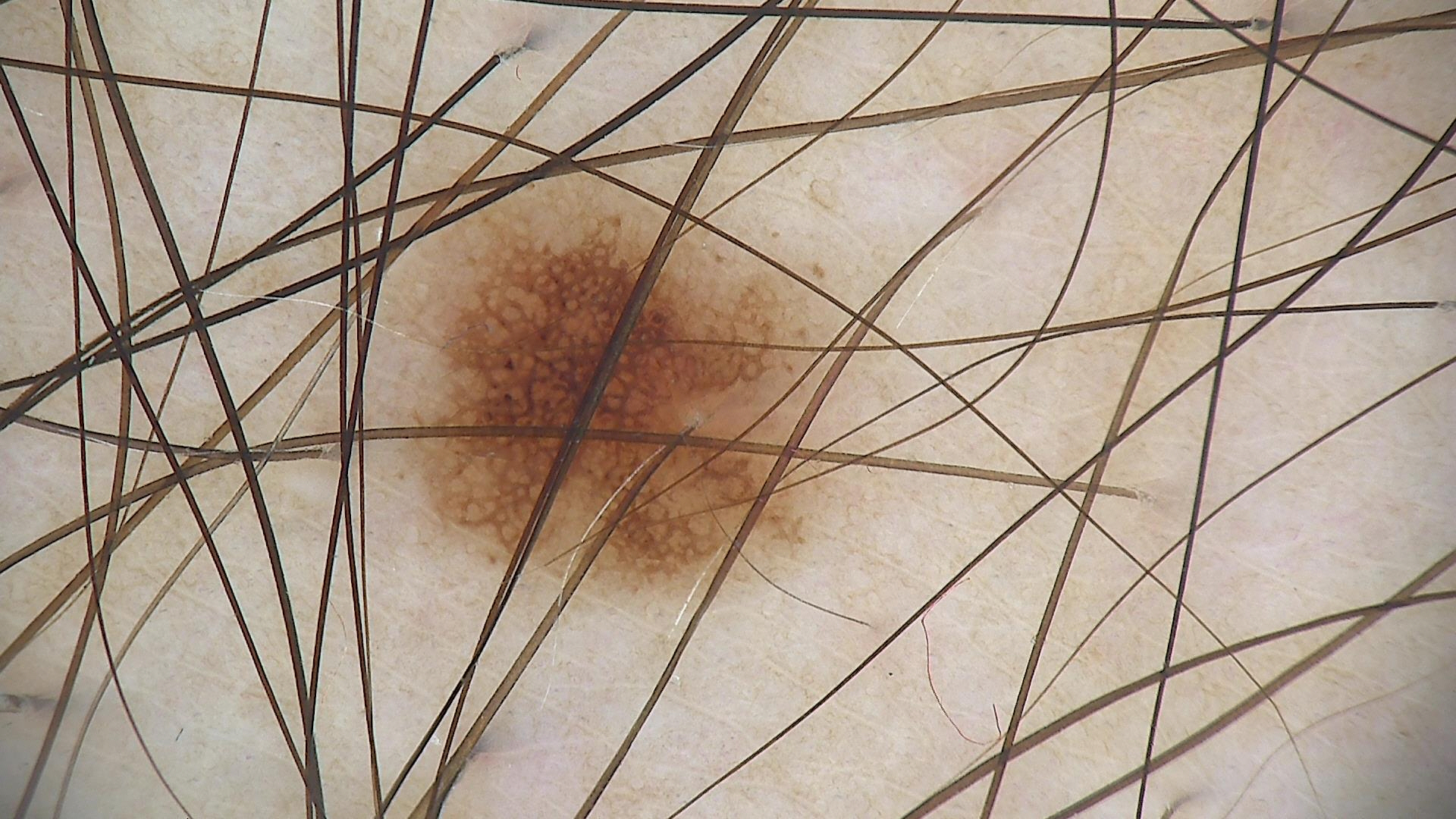A dermoscopy image of a single skin lesion. The diagnostic label was a dysplastic junctional nevus.